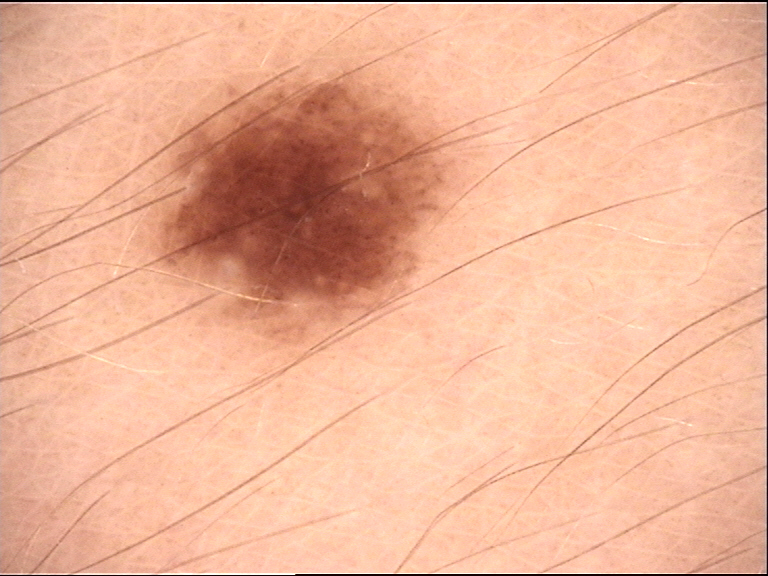A skin lesion imaged with a dermatoscope.
Consistent with a banal lesion — a junctional nevus.